Contact-polarized dermoscopy of a skin lesion — 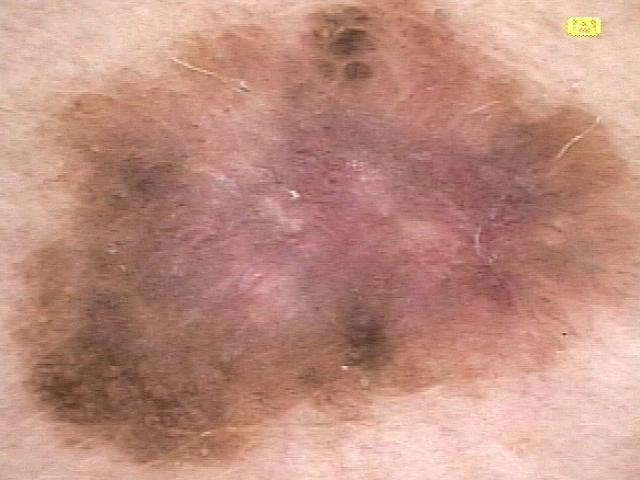Clinical context:
The lesion was found on the trunk (the posterior trunk).
Diagnosis:
Histopathology confirmed a benign, melanocytic lesion — a nevus.